The photograph is a close-up of the affected area: 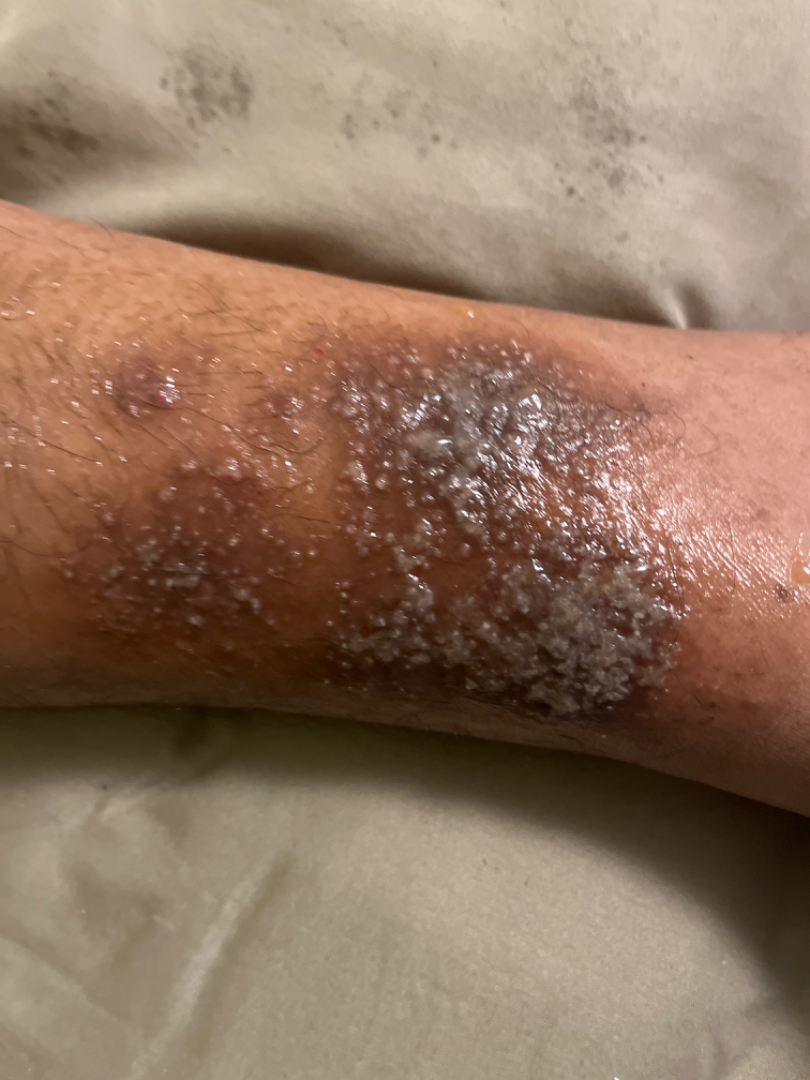{
  "differential": {
    "leading": [
      "Herpes Simplex"
    ],
    "considered": [
      "Allergic Contact Dermatitis"
    ]
  }
}